A smartphone photograph of a skin lesion — 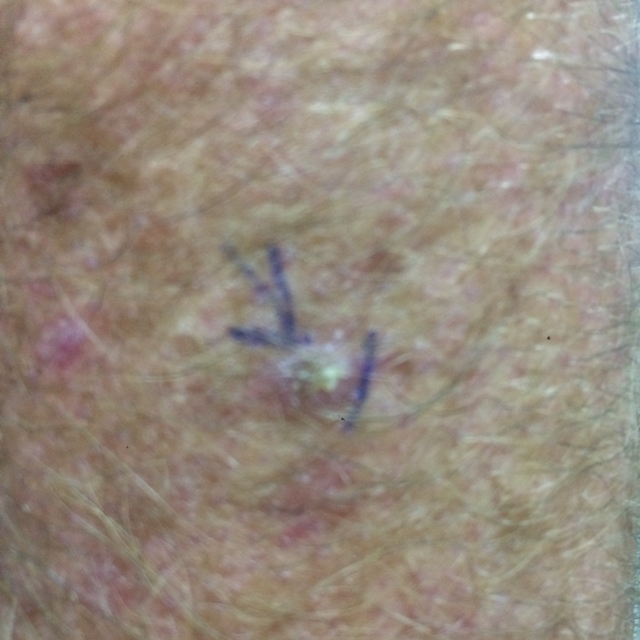Case:
• location · an arm
• reported symptoms · itching, elevation / no change in appearance, no growth
• assessment · actinic keratosis (clinical consensus)